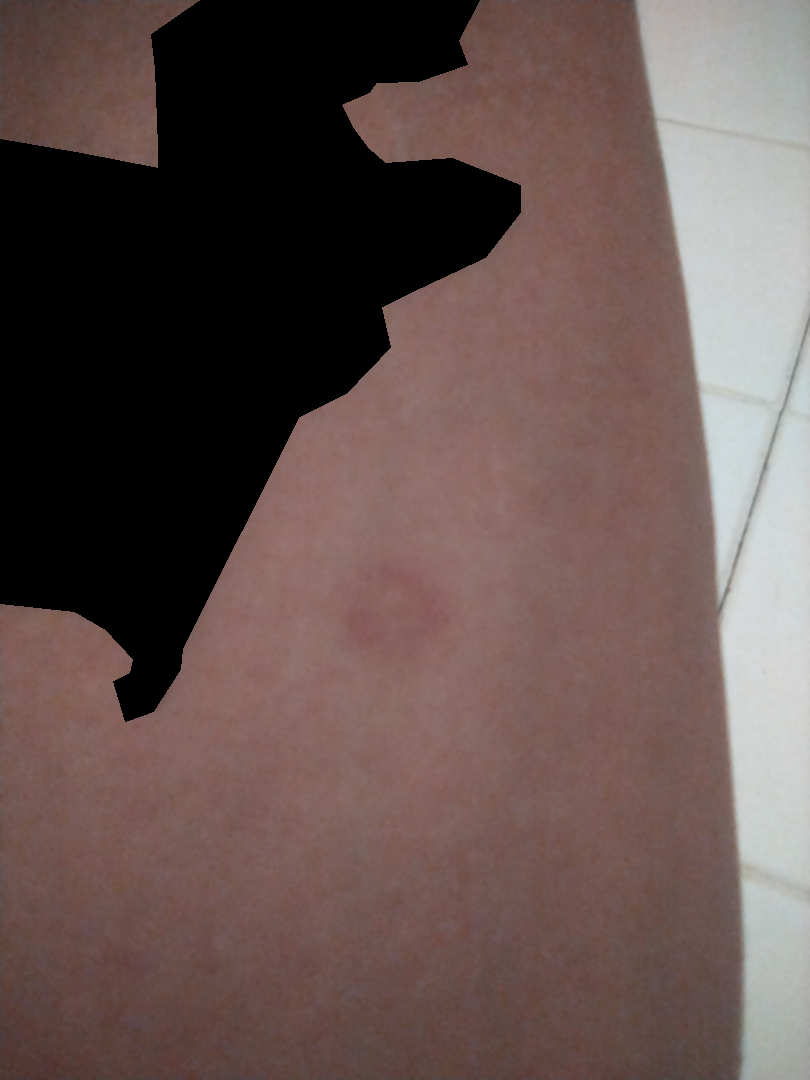Q: What was the assessment?
A: indeterminate
Q: What symptoms does the patient report?
A: bothersome appearance
Q: Fitzpatrick or Monk tone?
A: Fitzpatrick phototype III
Q: Any systemic symptoms?
A: none reported
Q: Anatomic location?
A: arm
Q: How does the patient describe it?
A: skin that appeared healthy to them
Q: What is the framing?
A: close-up
Q: Texture?
A: flat